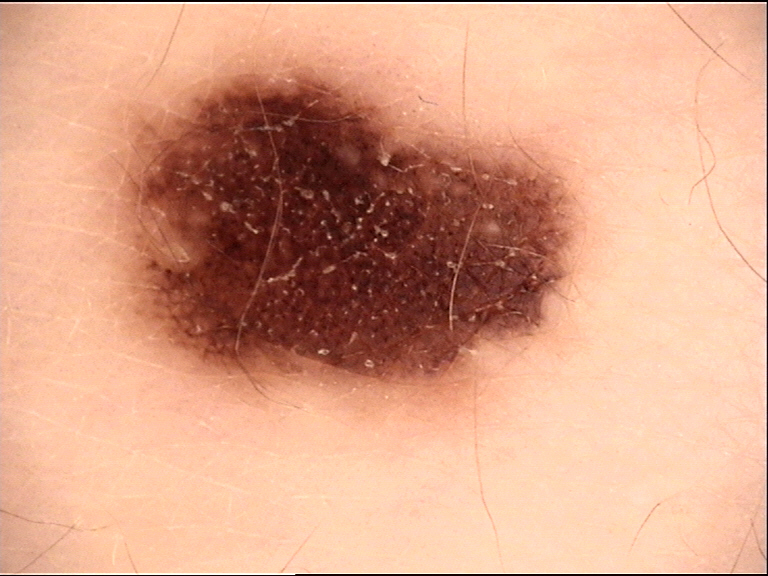{
  "lesion_type": {
    "main_class": "banal",
    "pattern": "junctional"
  },
  "diagnosis": {
    "name": "congenital junctional nevus",
    "code": "cjb",
    "malignancy": "benign",
    "super_class": "melanocytic",
    "confirmation": "expert consensus"
  }
}